By history, prior skin cancer (patient or family), prior malignancy (patient or family), alcohol use, and no pesticide exposure; recorded as skin type III; a smartphone photograph of a skin lesion; a male subject in their early 40s.
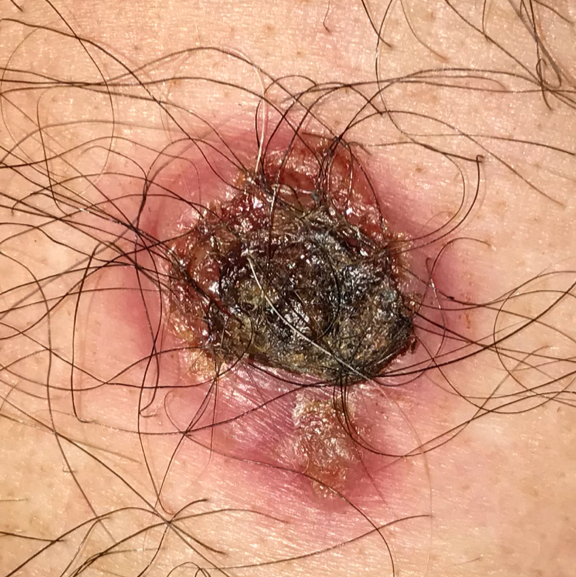Notes:
- body site: the chest
- size: approx. 30 × 25 mm
- symptoms: change in appearance, bleeding, growth, elevation / no itching
- pathology: basal cell carcinoma (biopsy-proven)